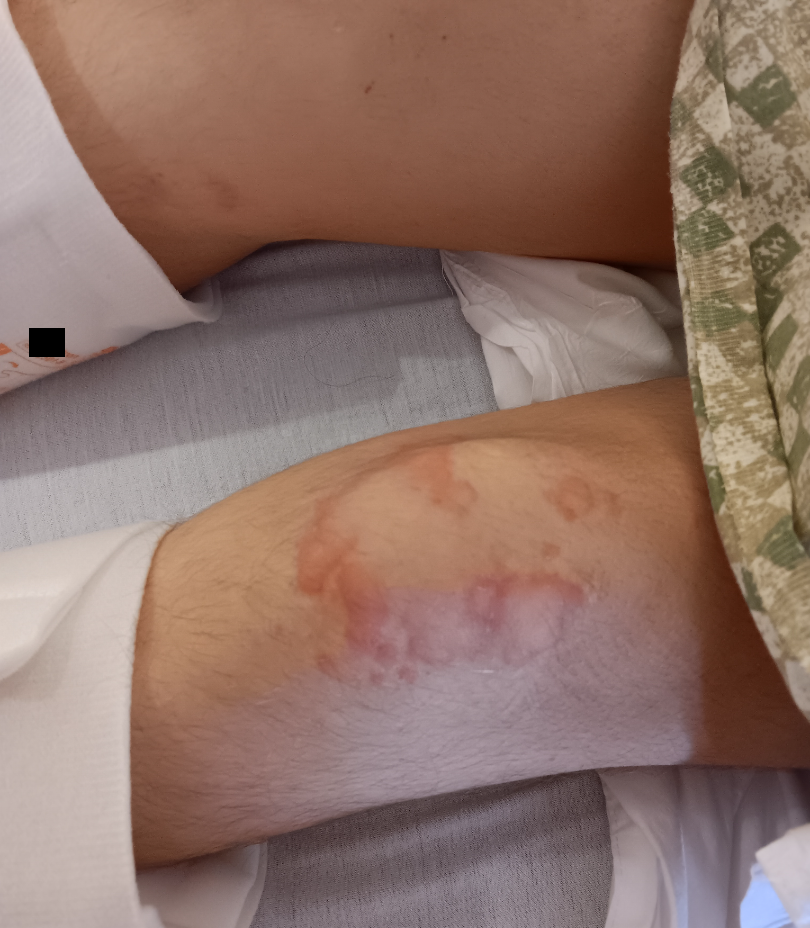Close-up view.
The patient did not report lesion symptoms.
Male contributor, age 18–29.
FST II; non-clinician graders estimated MST 2 or 4.
Self-categorized by the patient as a rash.
Reported duration is about one day.
Rheumatoid nodule (primary); gouty tophi (considered); Granuloma annulare (considered).